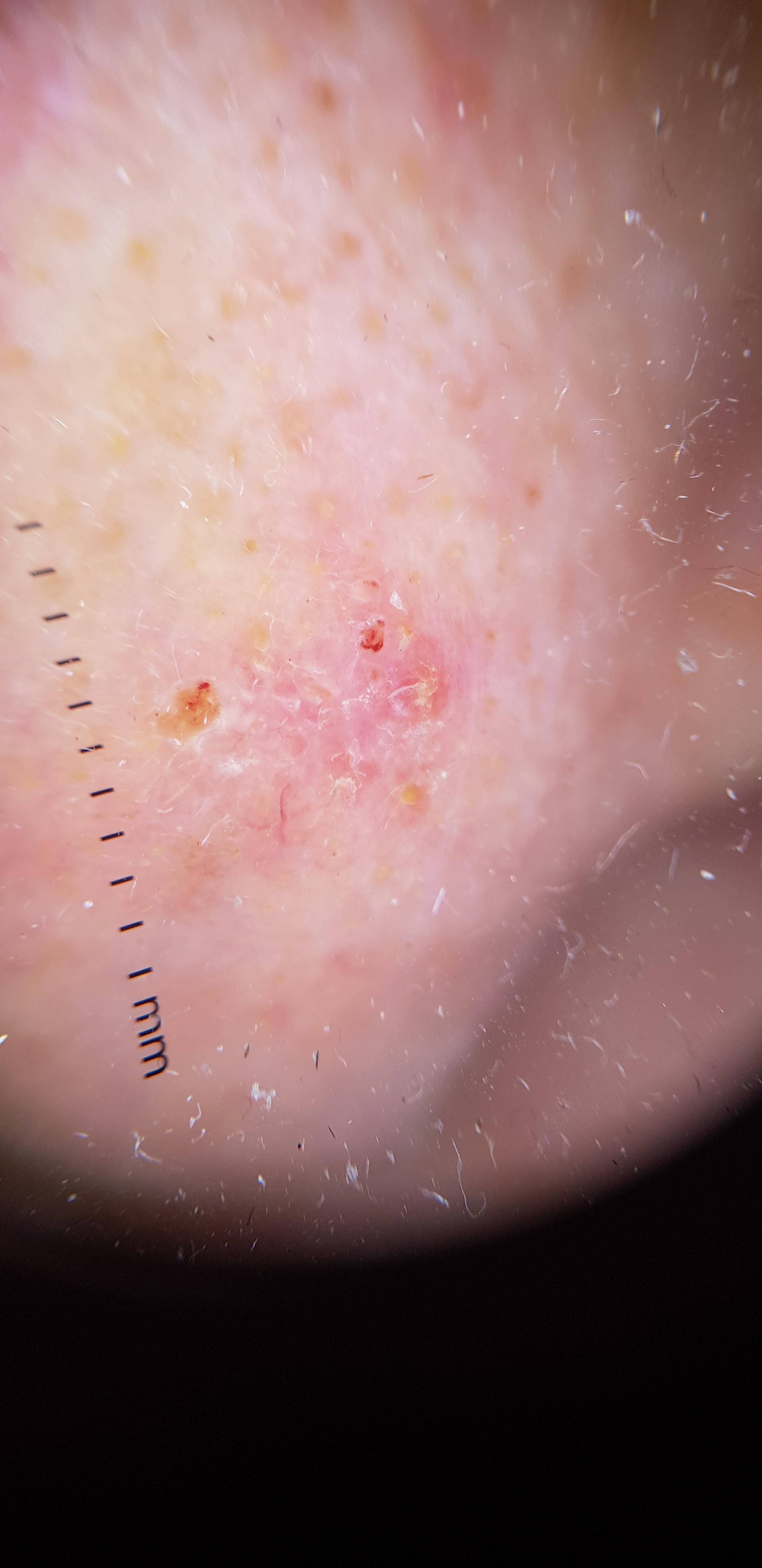patient = female, in their mid- to late 70s
skin type = II
location = the head or neck
pathology = Basal cell carcinoma (biopsy-proven)